The patient says their skin reddens with sun exposure · dermoscopy of a skin lesion · a moderate number of moles by the patient's own estimate · imaged for a research study, with no referral diagnosis recorded · a female subject aged 20: 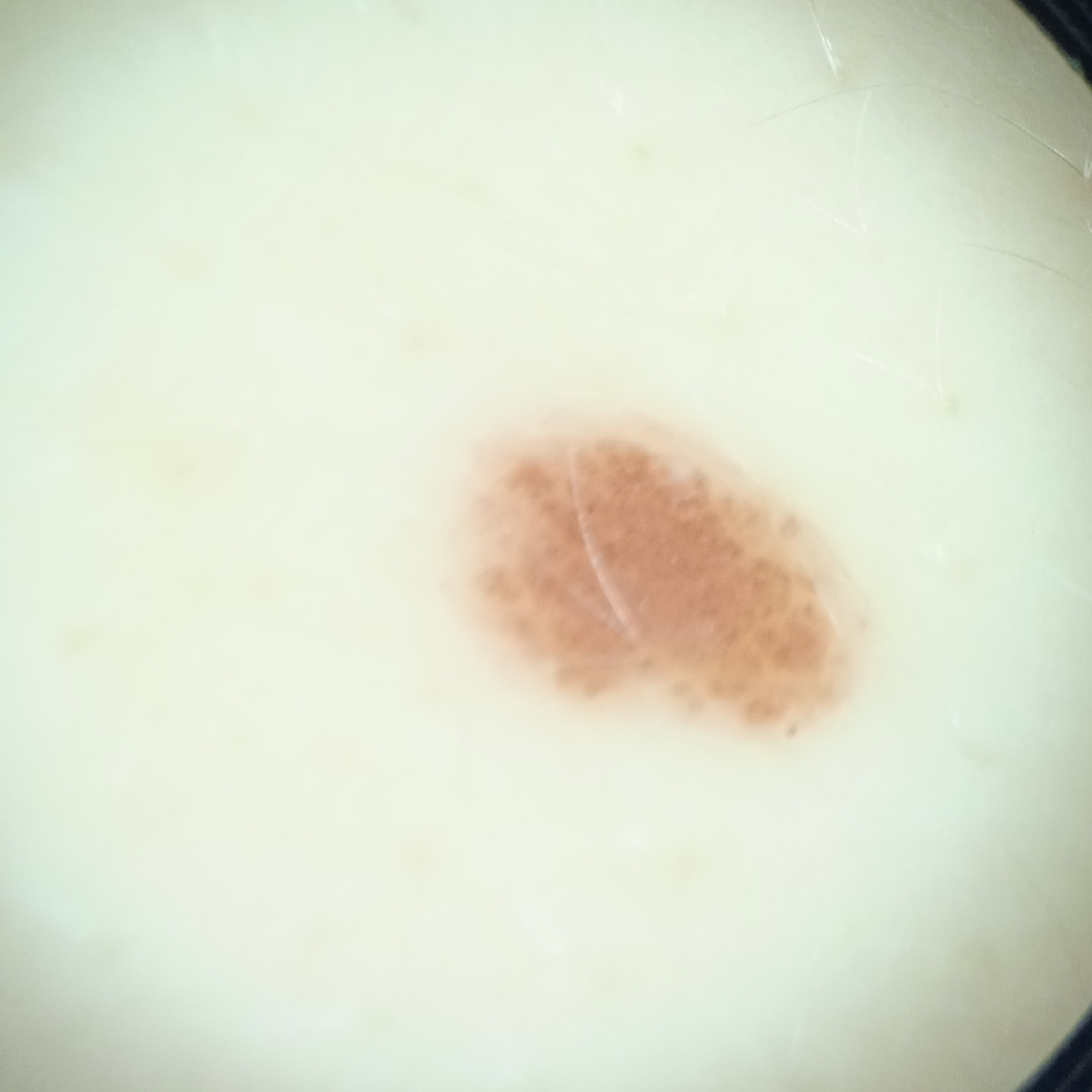site = the torso; diameter = 5.1 mm; assessment = melanocytic nevus (dermatologist consensus).